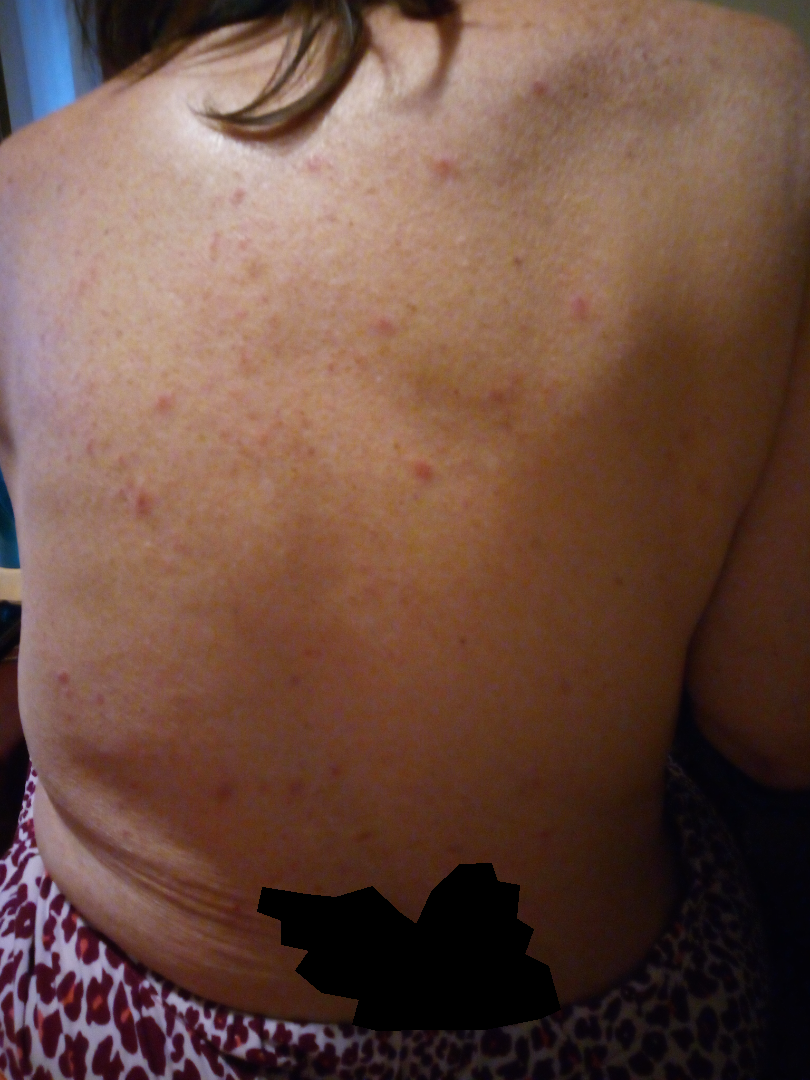Review: The dermatologist could not determine a likely condition from the photograph alone. Patient information: The photo was captured at a distance. Located on the arm, front of the torso, leg, back of the torso, sole of the foot, top or side of the foot and head or neck.